A clinical close-up photograph of a skin lesion; a patient in their 60s: 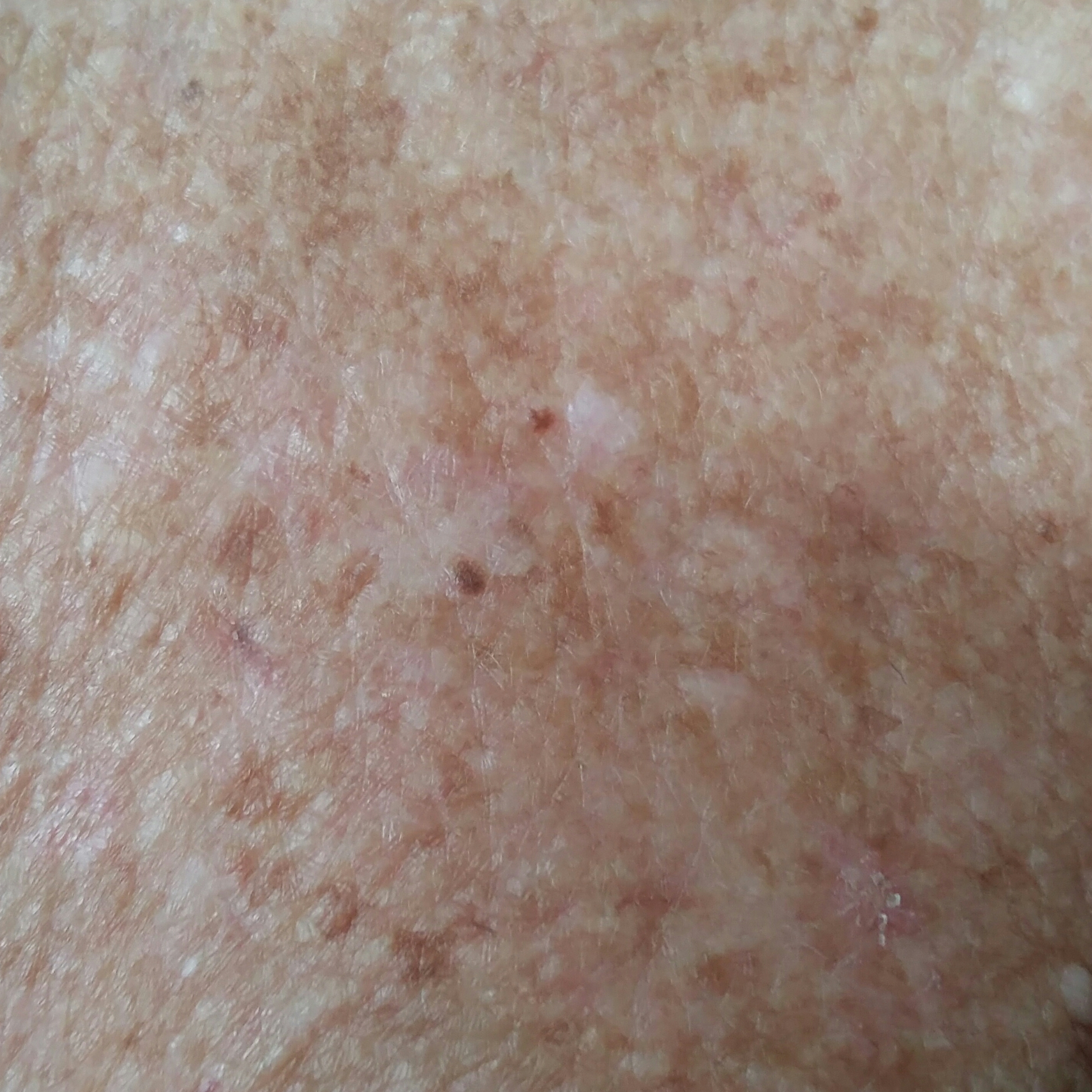| field | value |
|---|---|
| region | the chest |
| symptoms | itching |
| diagnosis | actinic keratosis (clinical consensus) |